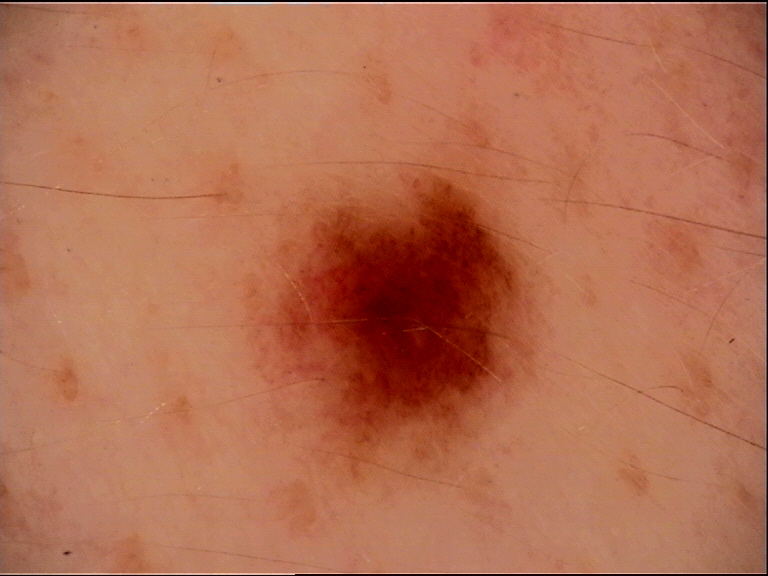The diagnosis was a dysplastic junctional nevus.